The patient reports a personal history of cancer · a dermoscopy image of a skin lesion · the patient says their skin reddens with sun exposure · the patient describes having few moles overall · collected as part of a research study, without a referral diagnosis · a male subject 78 years old — 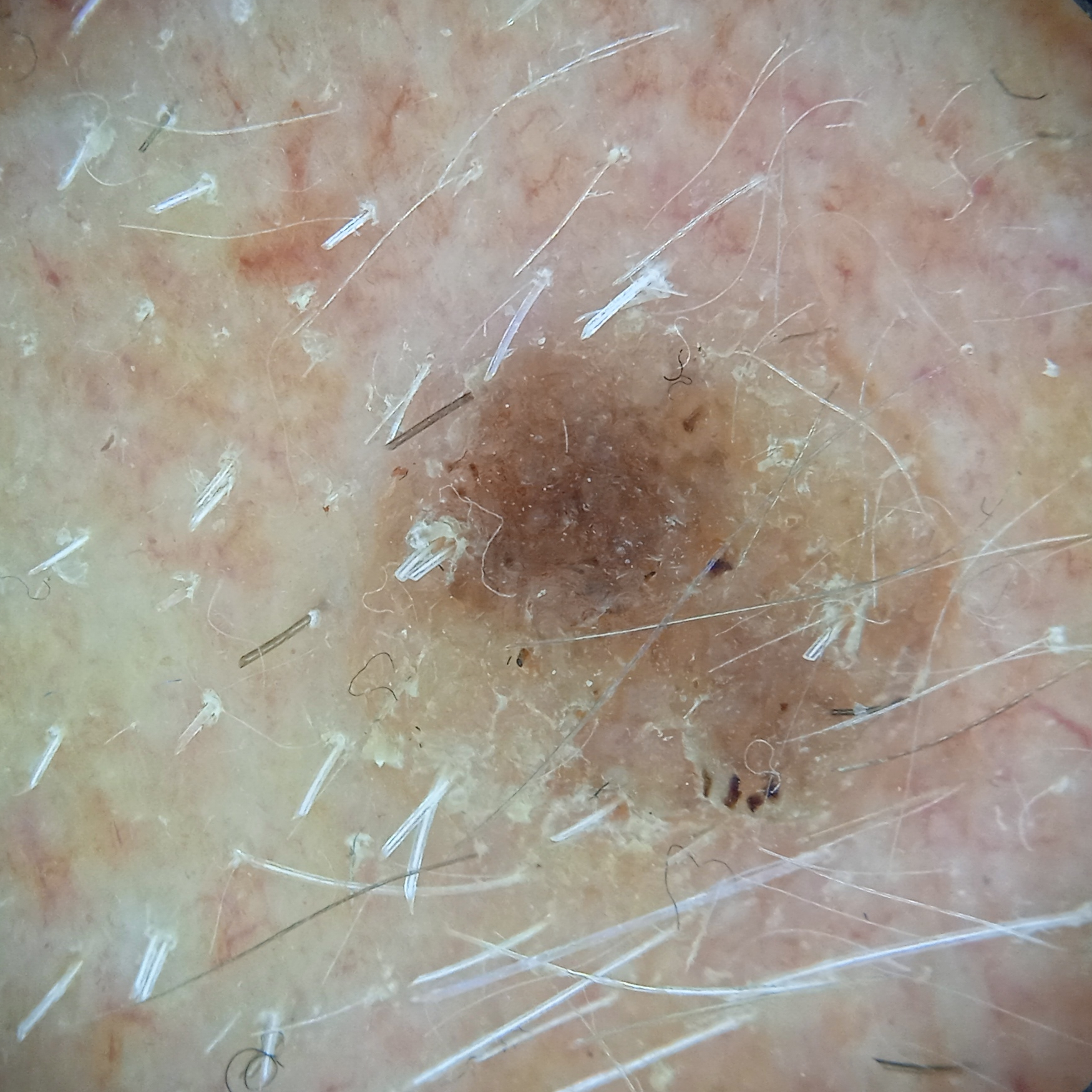<lesion>
<lesion_location>the face</lesion_location>
<lesion_size>
<diameter_mm>6.8</diameter_mm>
</lesion_size>
<diagnosis>
<name>seborrheic keratosis</name>
<malignancy>benign</malignancy>
</diagnosis>
</lesion>